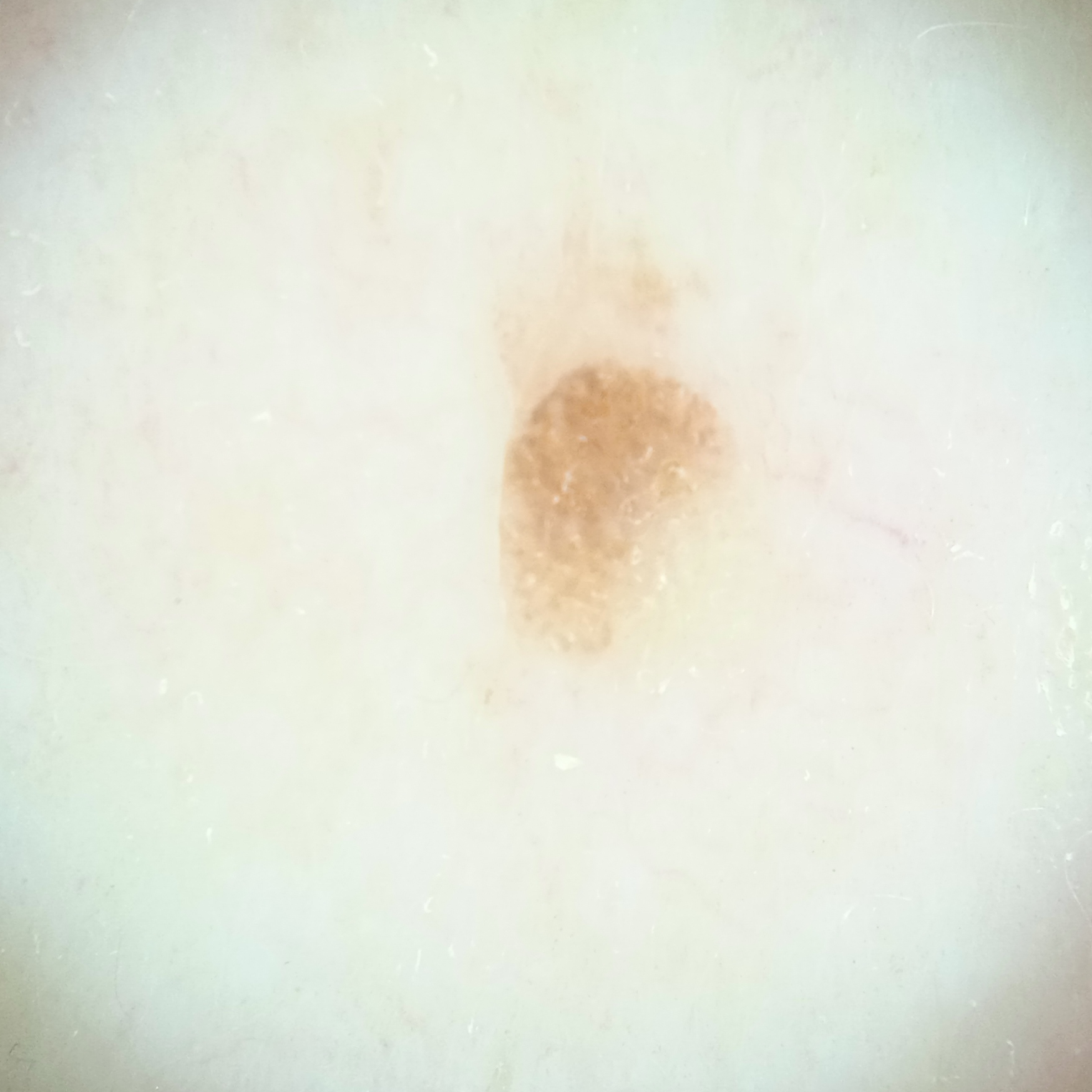The diagnostic impression was a seborrheic keratosis.